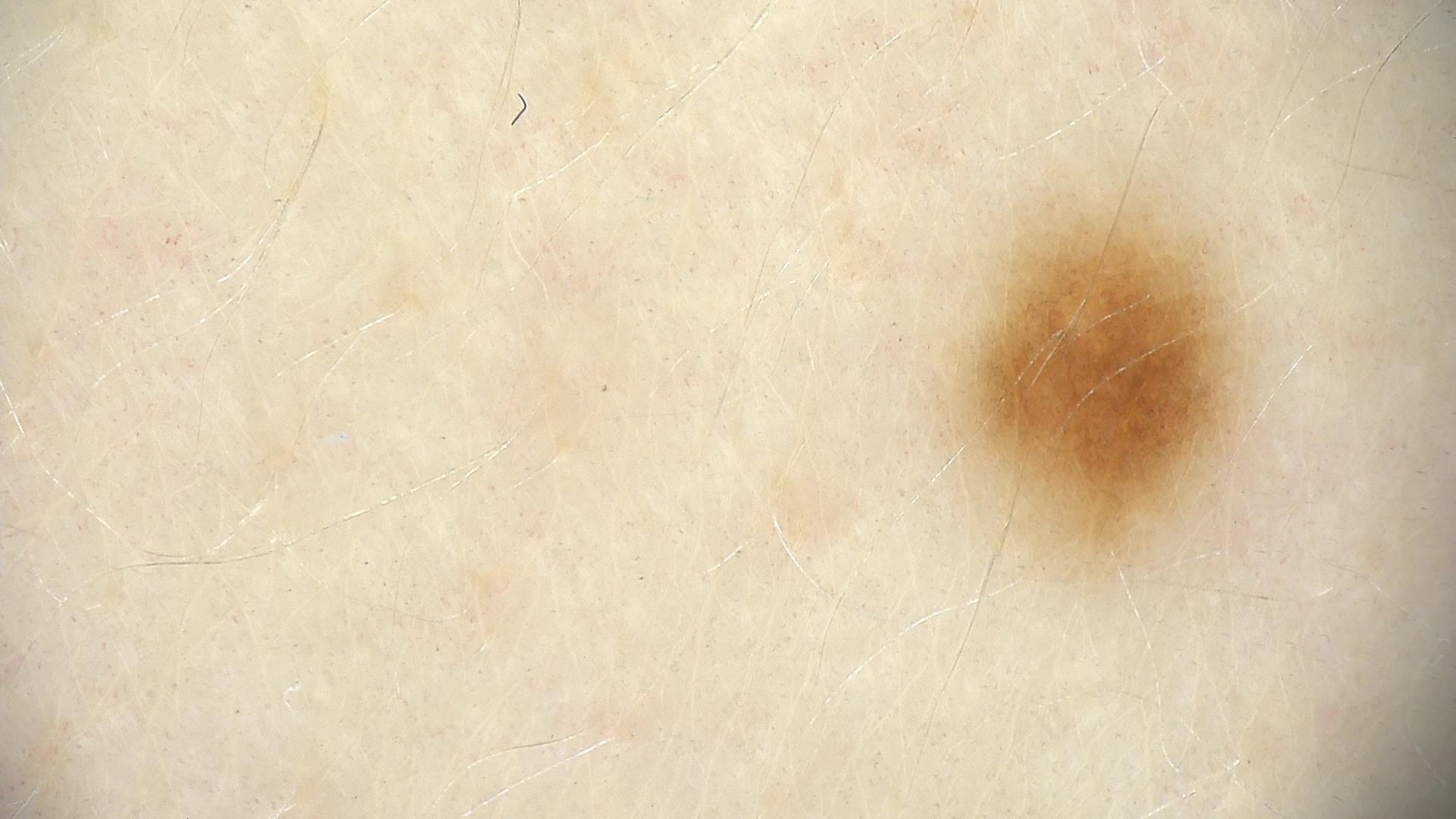A dermoscopic image of a skin lesion. Consistent with a dysplastic junctional nevus.